An image taken at an angle · the affected area is the leg:
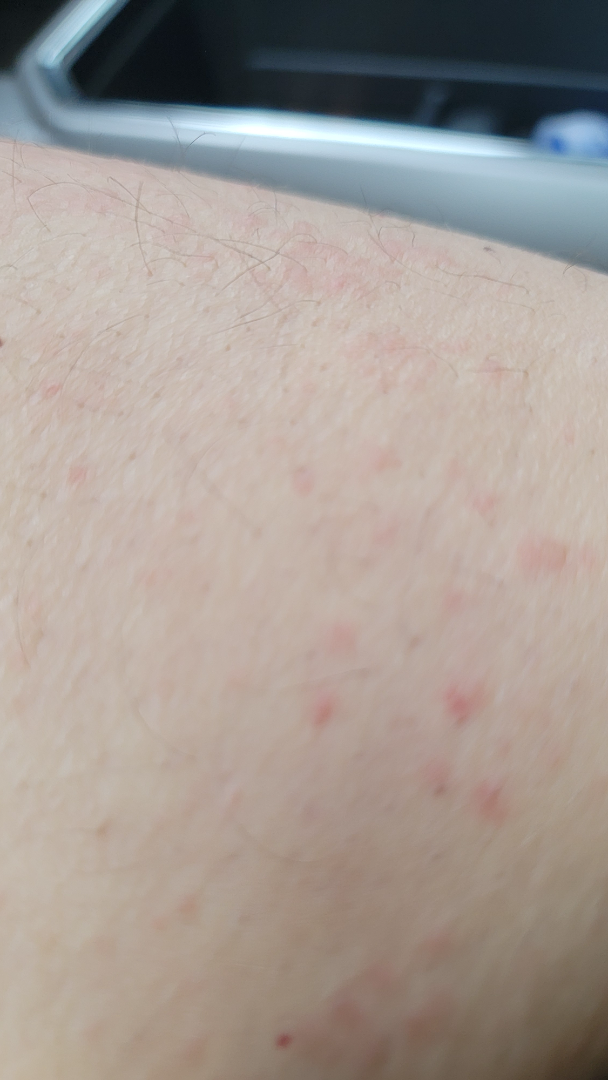Q: What conditions are considered?
A: Urticaria (considered); Eczema (considered); Allergic Contact Dermatitis (considered)